A dermoscopic image of a skin lesion.
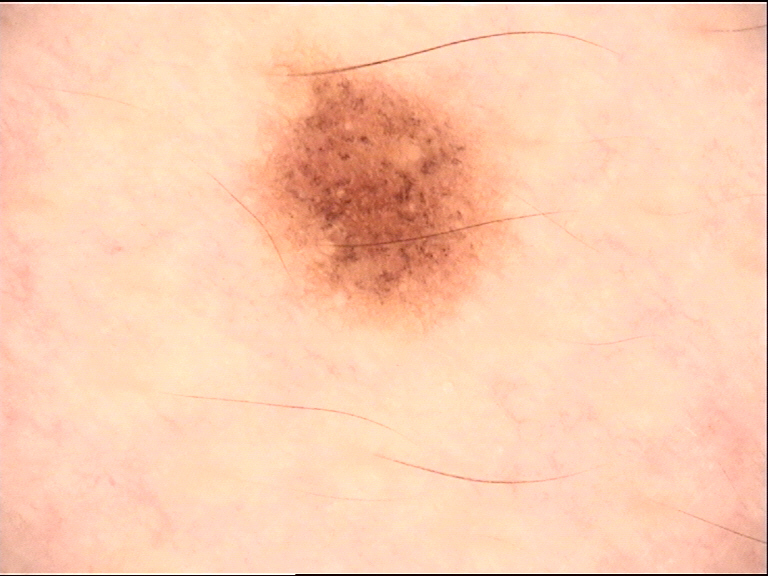The diagnosis was a banal lesion — a junctional nevus.